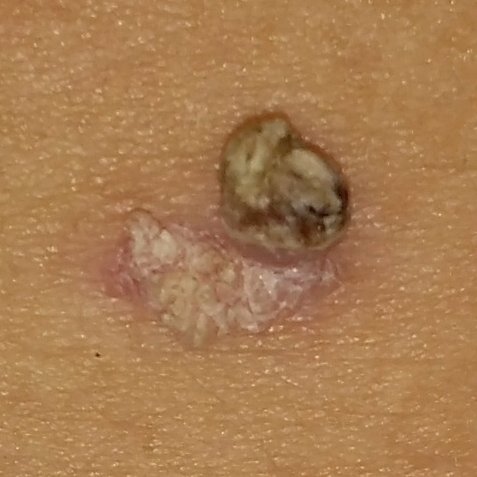Findings:
* subject · female, in their 20s
* image · clinical photograph
* anatomic site · the back
* reported symptoms · elevation / no growth
* diagnosis · actinic keratosis (biopsy-proven)